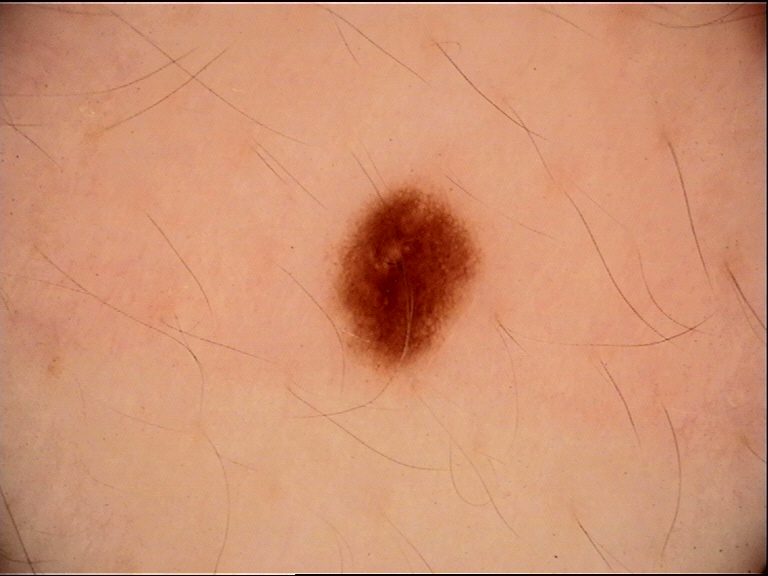A dermoscopic image of a skin lesion.
Consistent with a benign lesion — a dysplastic junctional nevus.